A dermoscopic photograph of a skin lesion.
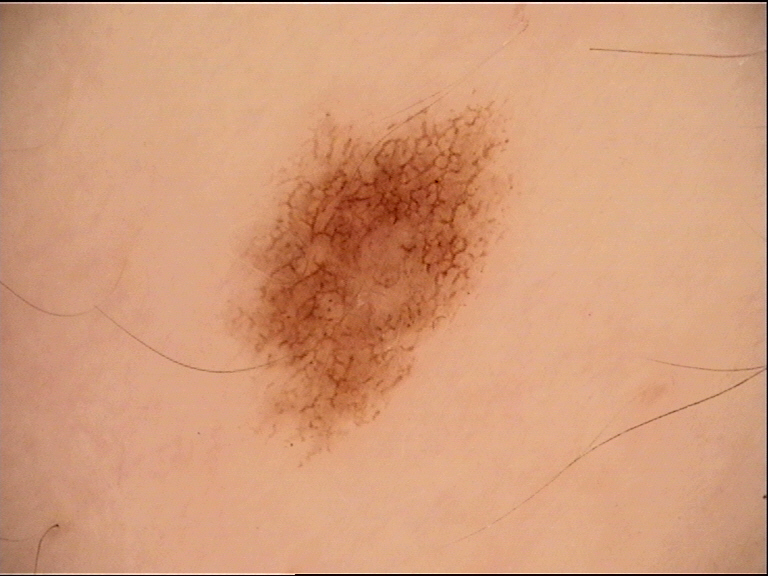Impression:
The diagnostic label was a dysplastic junctional nevus.